The lesion is associated with itching and bothersome appearance. Texture is reported as raised or bumpy. The photograph was taken at an angle. No associated systemic symptoms reported. The affected area is the arm. The patient considered this a rash. The condition has been present for less than one week. Male patient, age 18–29:
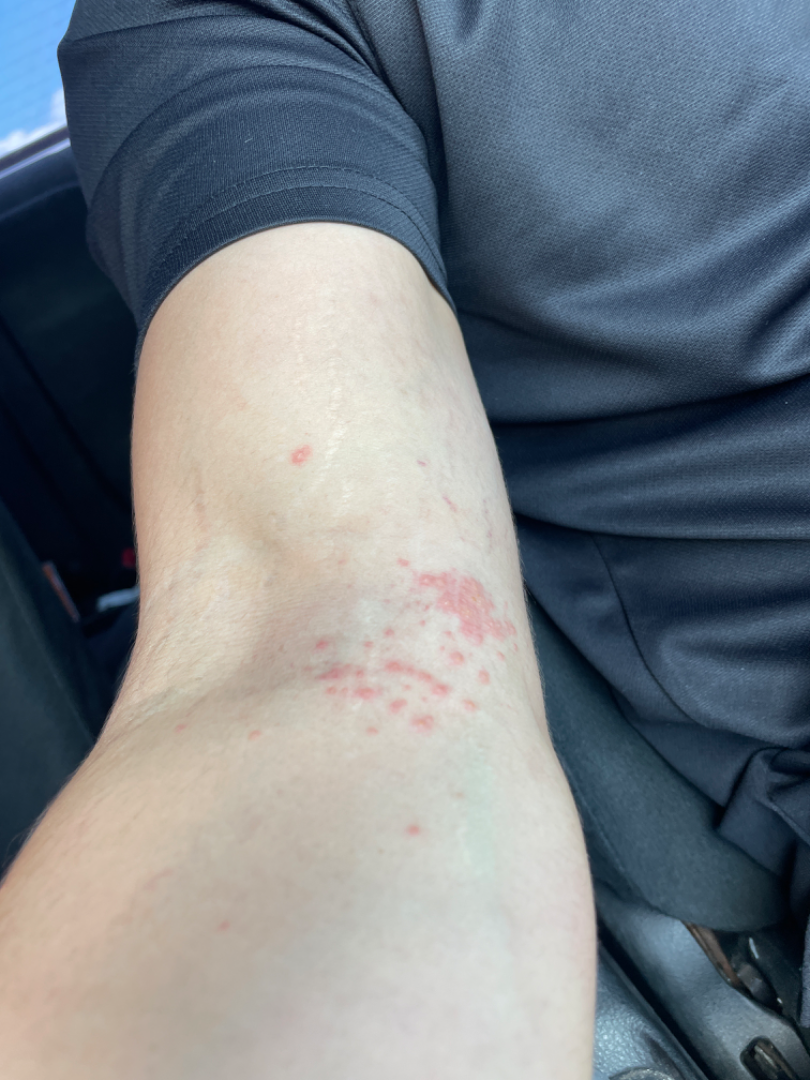On photographic review: in keeping with Allergic Contact Dermatitis.